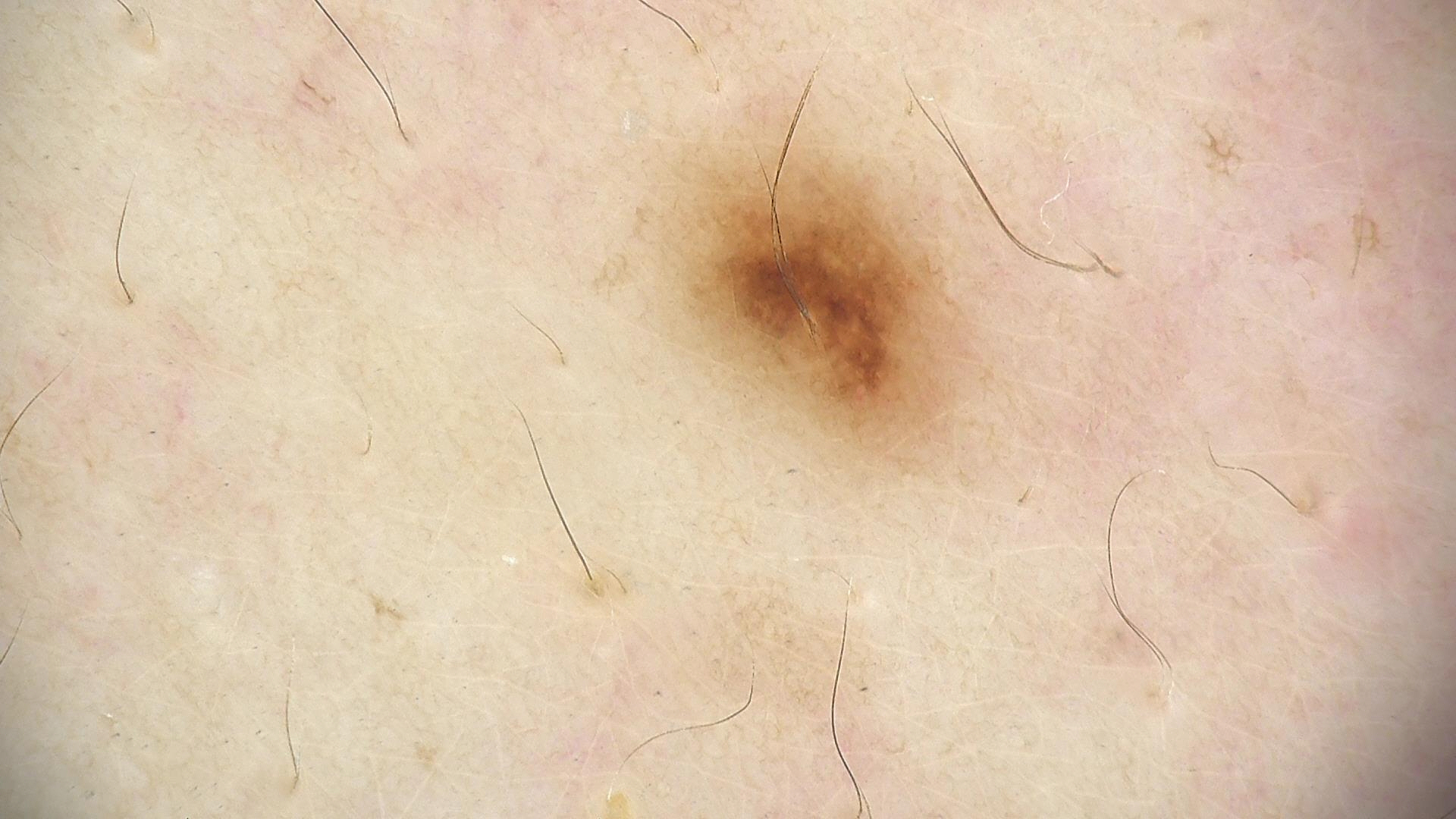diagnostic label — dysplastic junctional nevus (expert consensus).